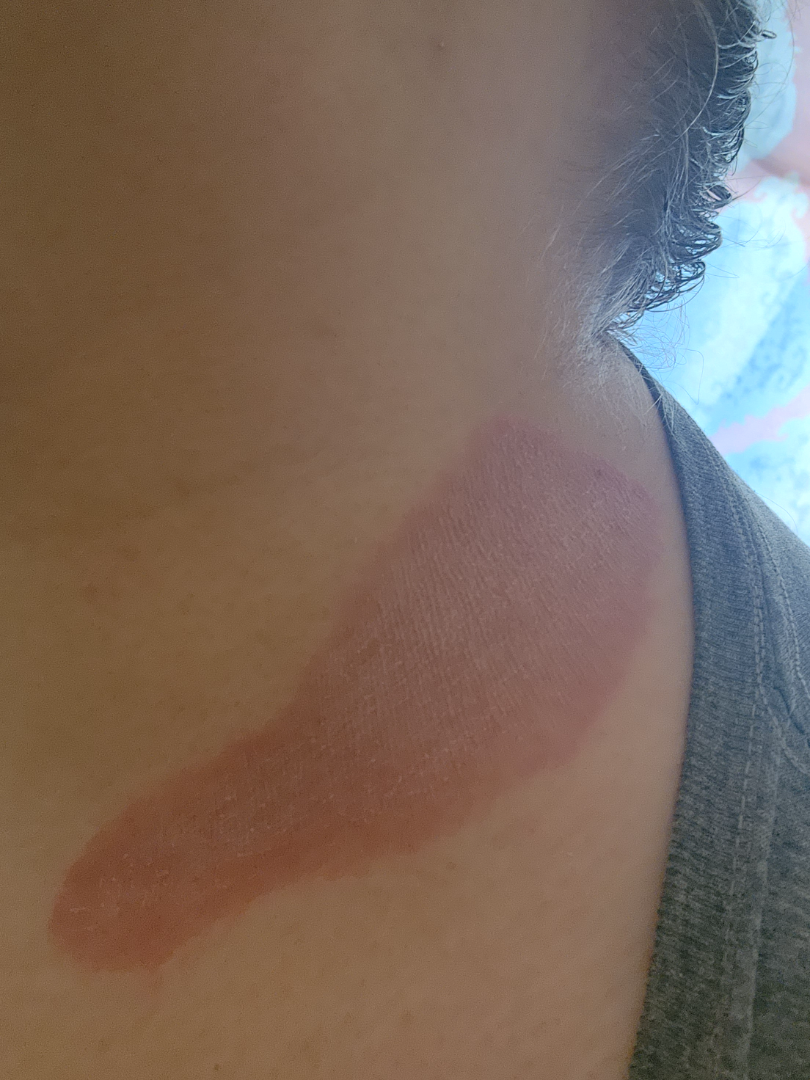patient describes the issue as: a rash
onset: three to twelve months
associated systemic symptoms: none reported
reported symptoms: burning, enlargement, itching and pain
patient: female, age 30–39
framing: at an angle
affected area: head or neck
differential diagnosis: Psoriasis, Burn erythema of neck and Allergic Contact Dermatitis were each considered, in no particular order